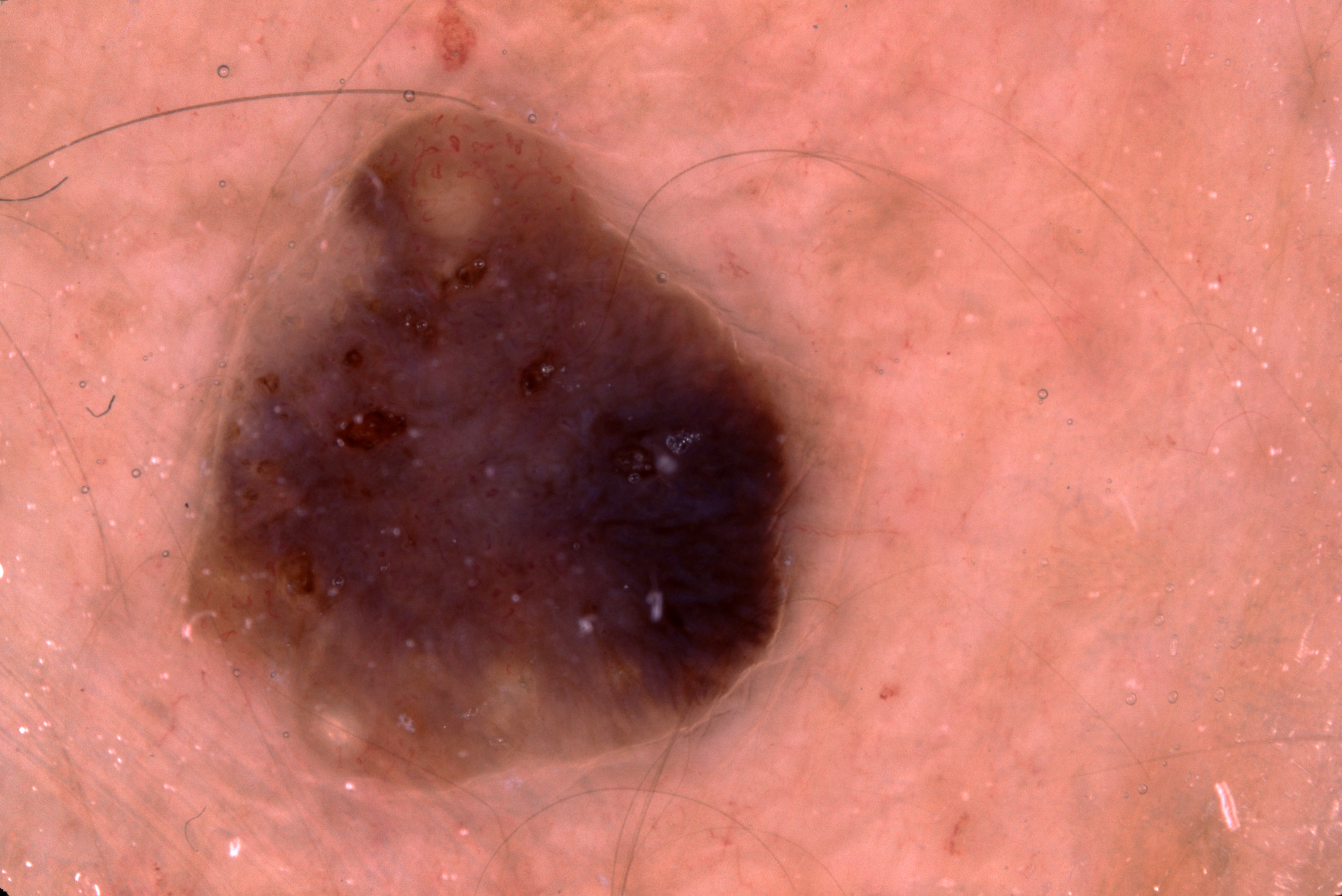Dermoscopy of a skin lesion. Dermoscopically, the lesion shows milia-like cysts; no negative network, pigment network, or streaks. In (x1, y1, x2, y2) order, the lesion spans bbox(189, 112, 807, 784). The diagnostic assessment was a seborrheic keratosis.